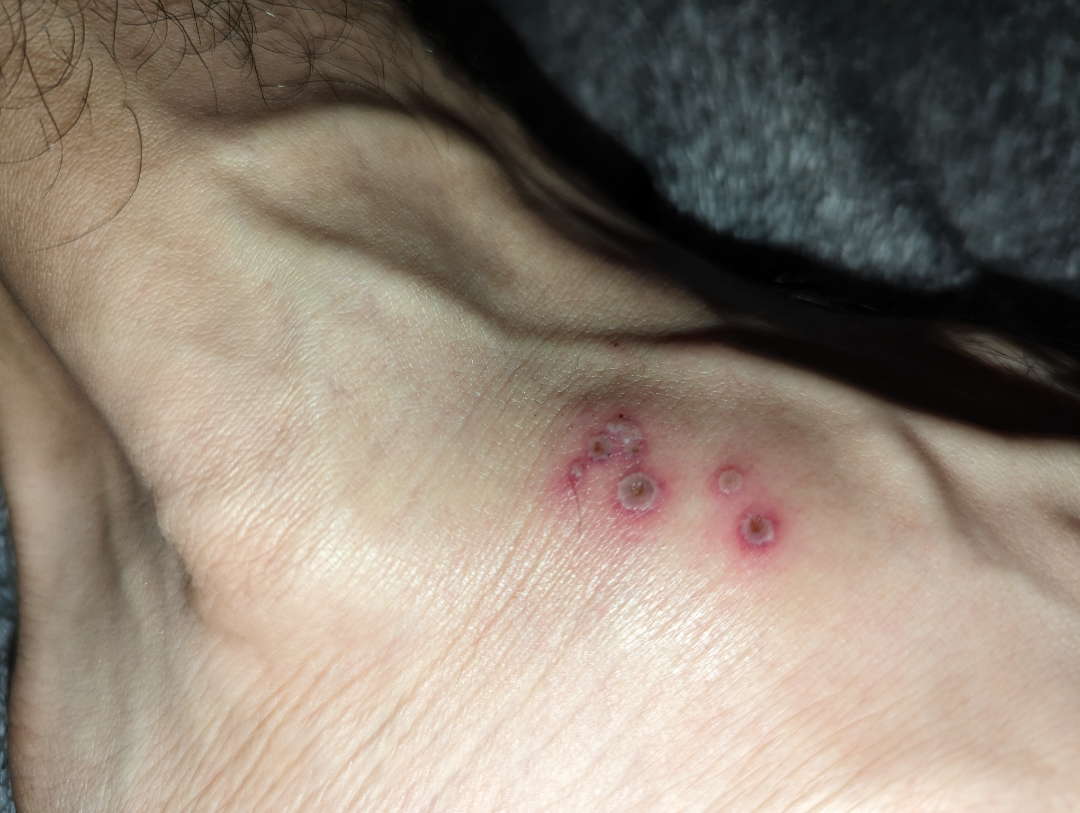{"body_site": "top or side of the foot", "shot_type": "close-up", "texture": "raised or bumpy", "duration": "less than one week", "patient_category": "a rash", "symptoms": "itching", "systemic_symptoms": "none reported", "differential": {"leading": ["Herpes Simplex"], "considered": ["Insect Bite"], "unlikely": ["Herpes Zoster"]}}